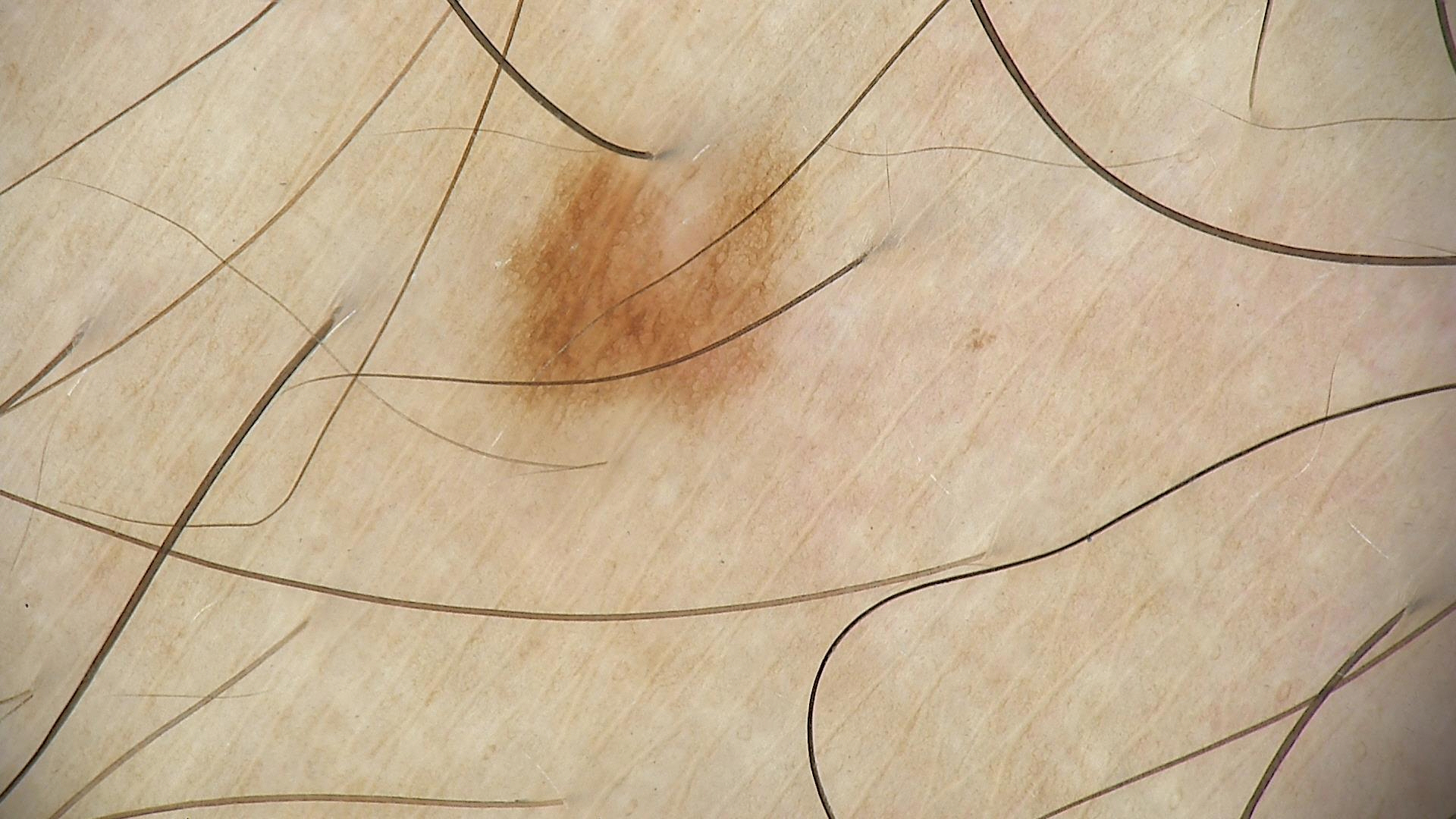Q: What was the diagnostic impression?
A: dysplastic junctional nevus (expert consensus)